A dermoscopic photograph of a skin lesion.
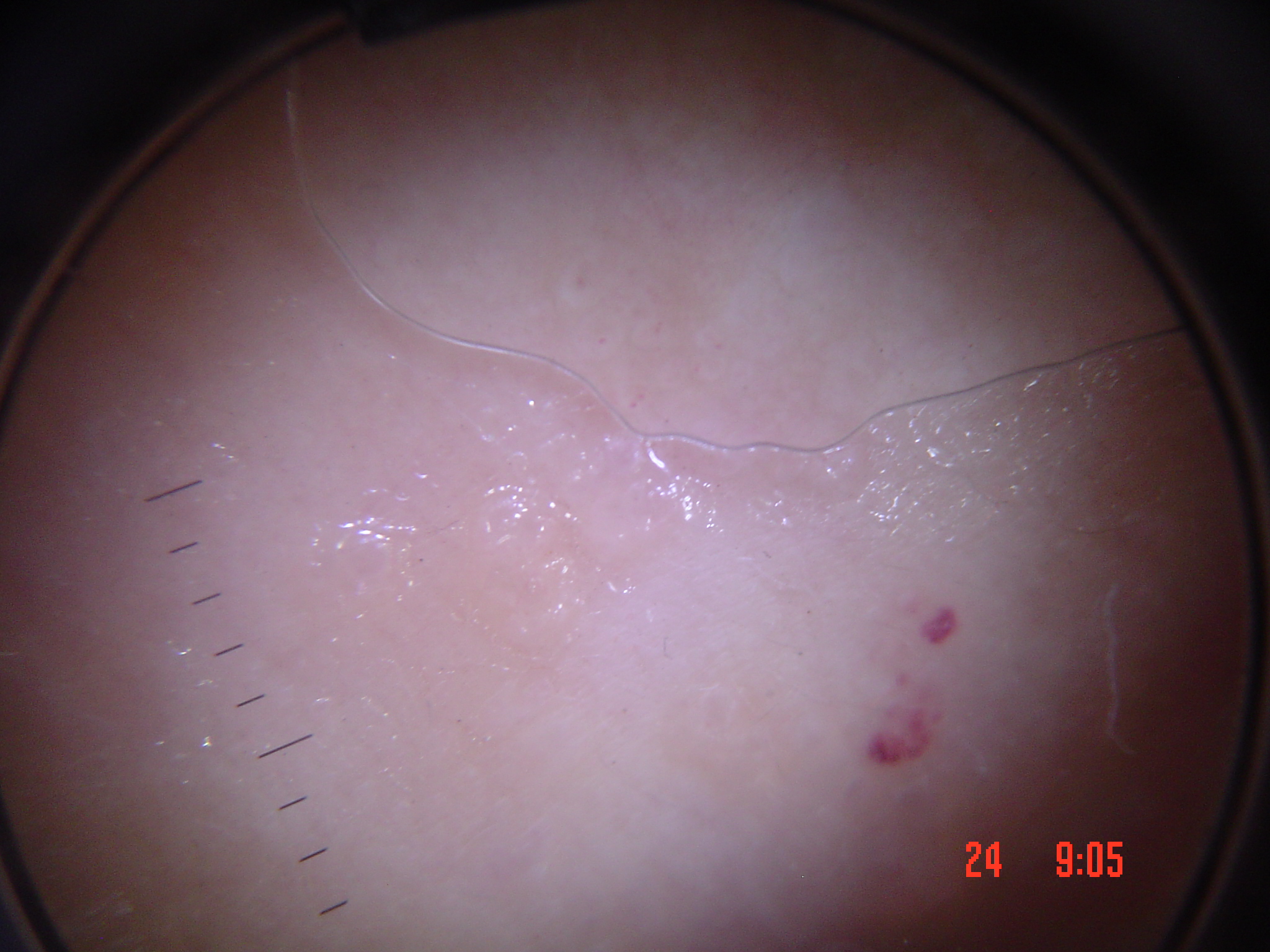The morphology is that of a vascular lesion. Classified as a benign lesion — a hemangioma.